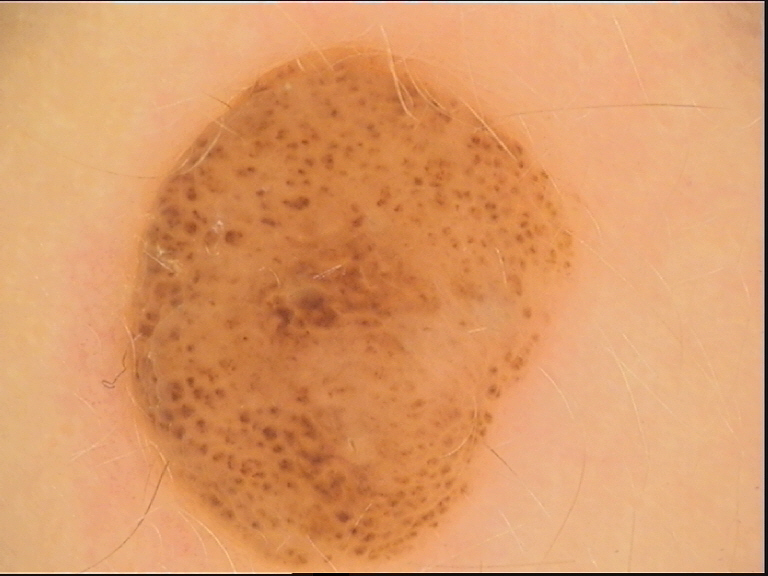Impression: Diagnosed as a compound nevus.